This is a close-up image; located on the arm, head or neck and leg.
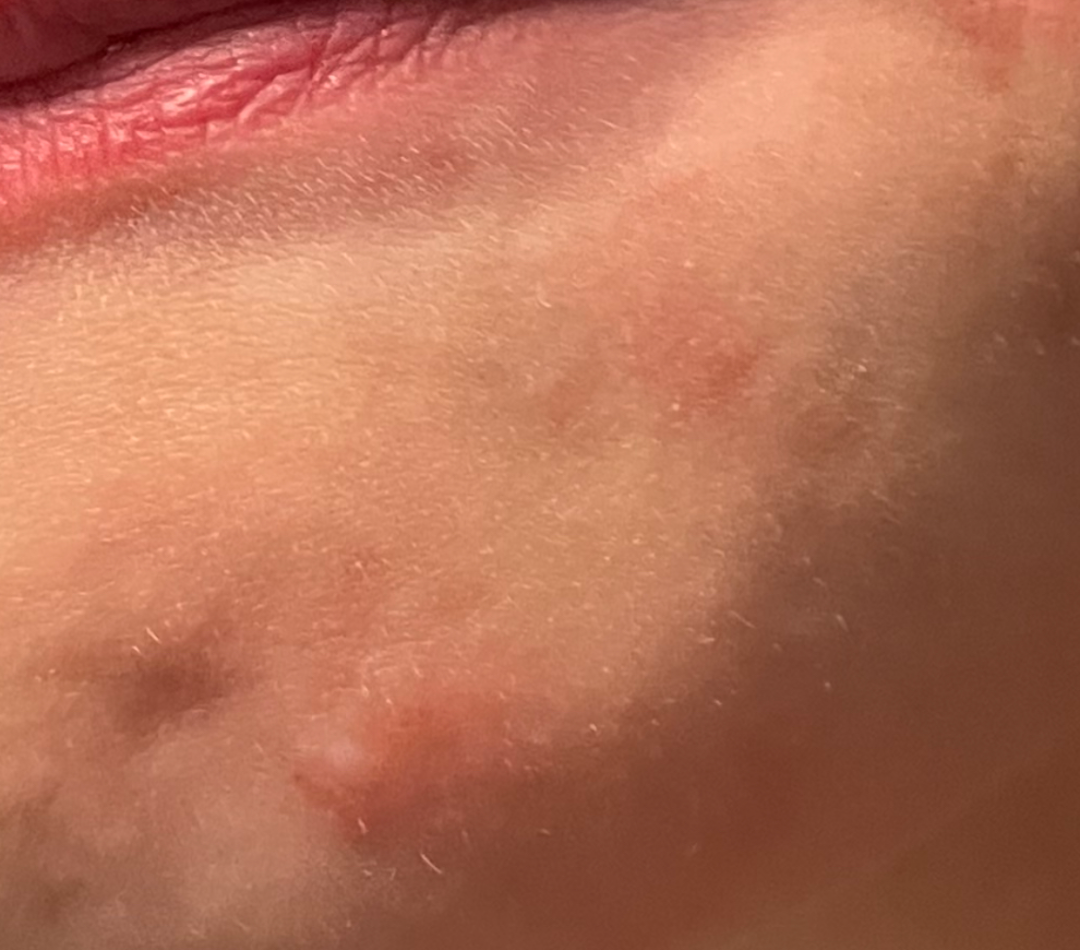The reviewer was unable to grade this case for skin condition.
Texture is reported as raised or bumpy.